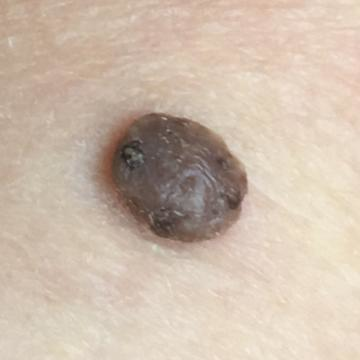A patient 86 years old.
The lesion is located on the back.
The patient reports that the lesion is elevated and has grown, but has not changed and does not itch.
The consensus clinical diagnosis was a benign skin lesion — a seborrheic keratosis.